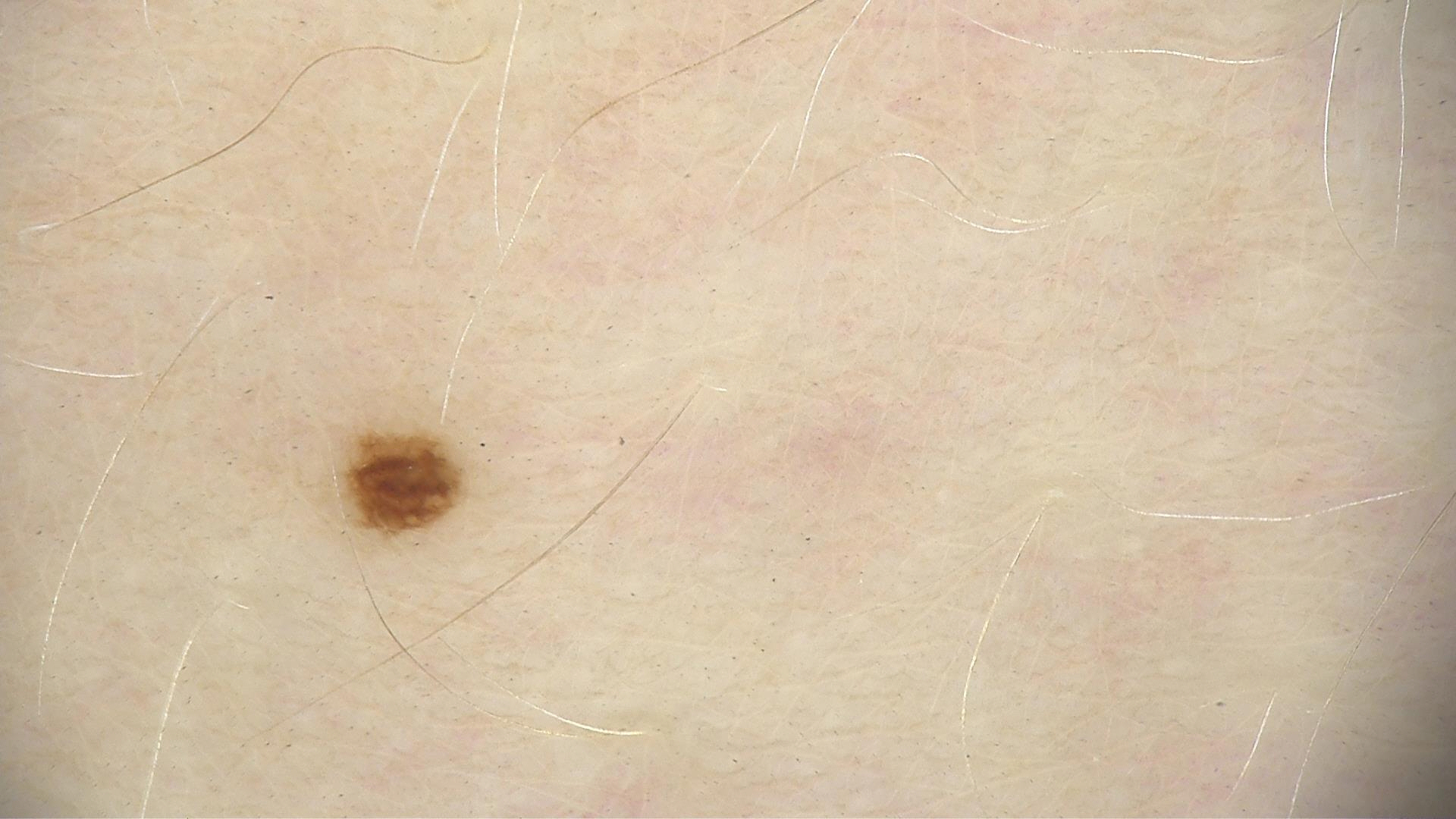{"image": "dermoscopy", "diagnosis": {"name": "dysplastic junctional nevus", "code": "jd", "malignancy": "benign", "super_class": "melanocytic", "confirmation": "expert consensus"}}